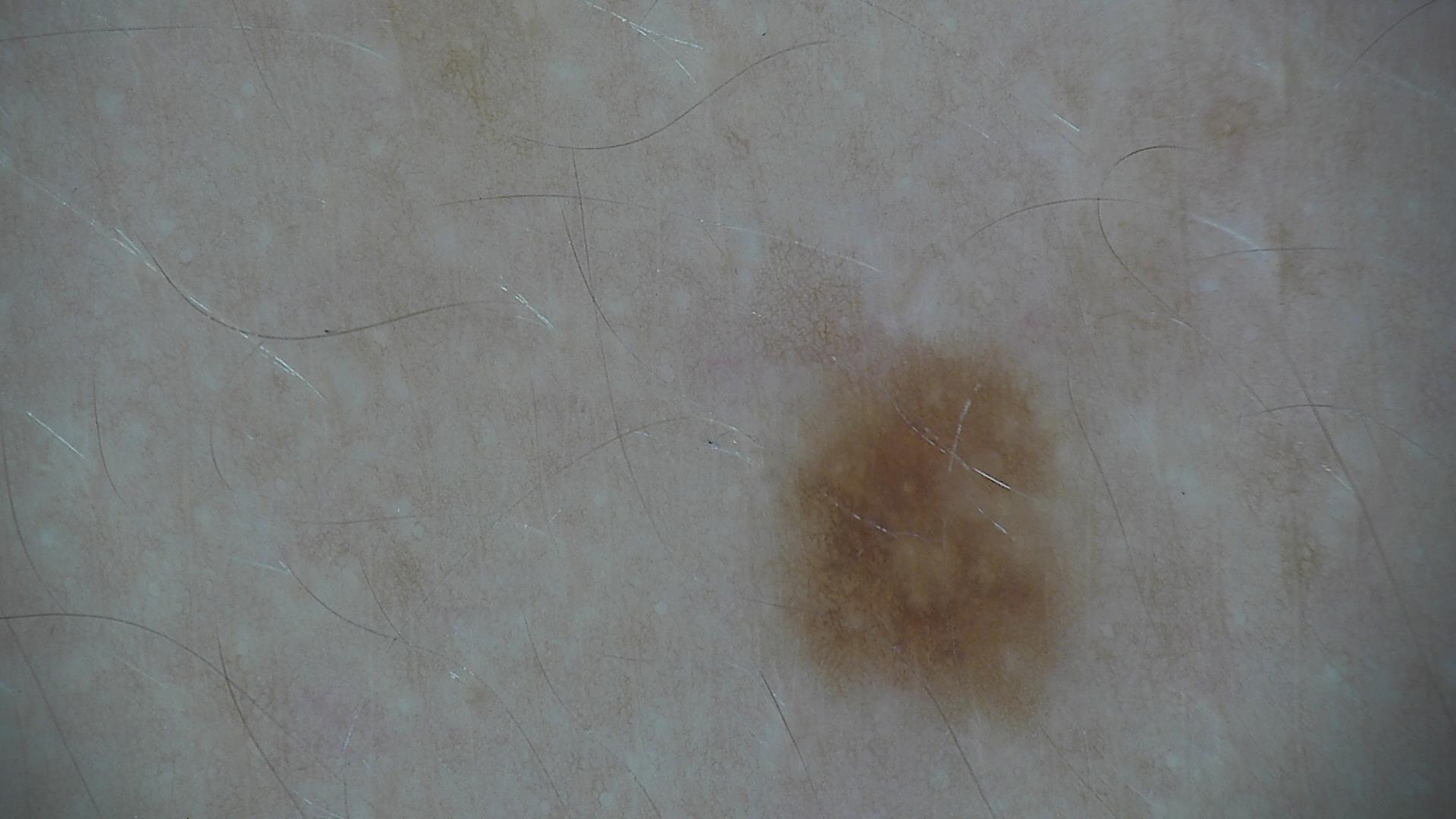A skin lesion imaged with a dermatoscope. The diagnostic label was a dysplastic junctional nevus.